A dermoscopic photograph of a skin lesion.
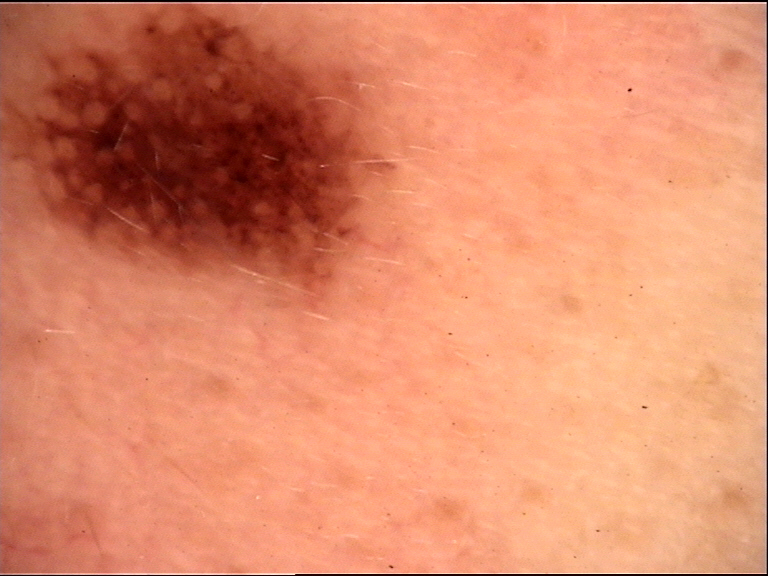<lesion>
<diagnosis>
<name>Miescher nevus</name>
<code>mcb</code>
<malignancy>benign</malignancy>
<super_class>melanocytic</super_class>
<confirmation>expert consensus</confirmation>
</diagnosis>
</lesion>